A dermoscopic image of a skin lesion.
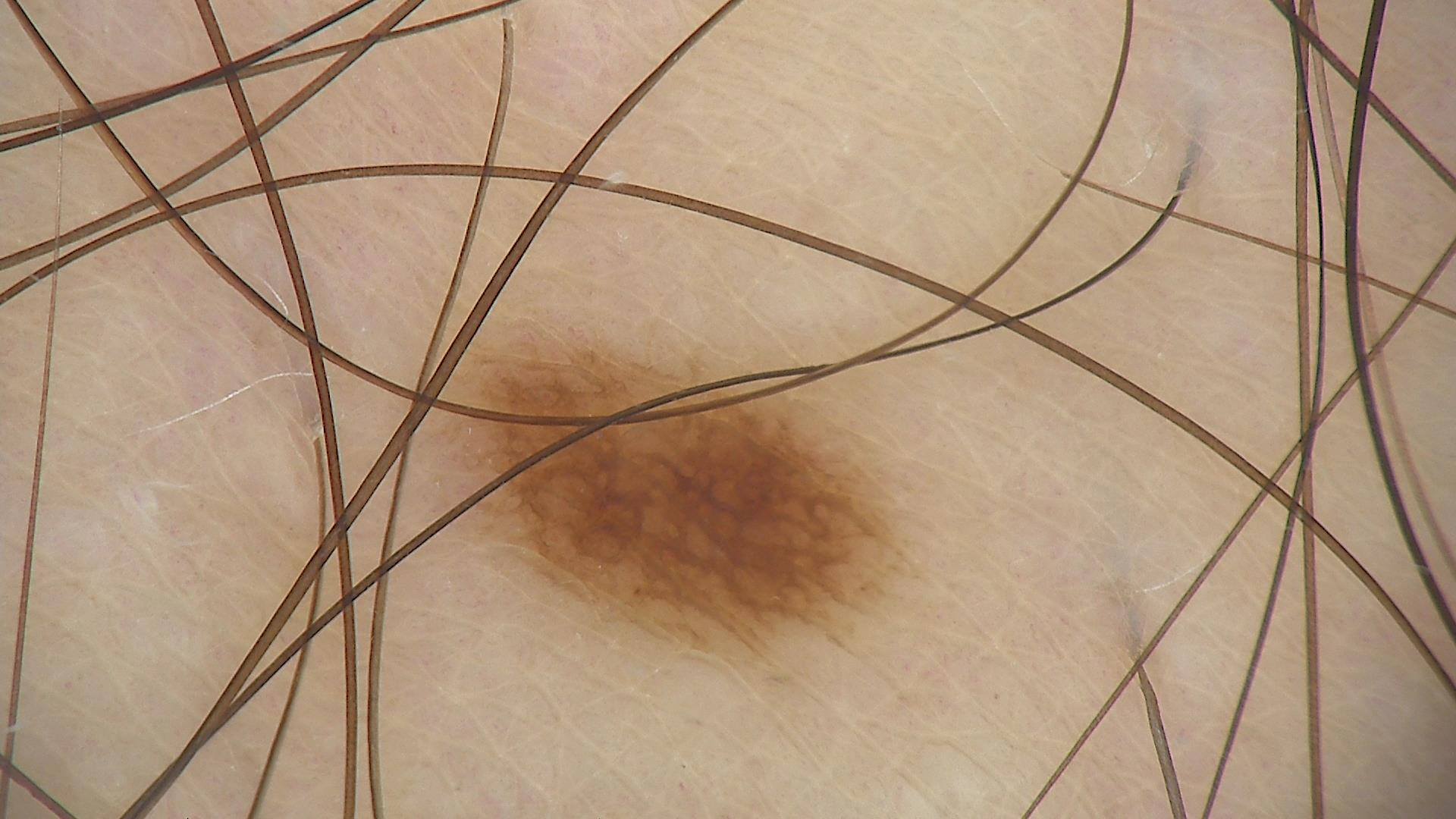– class: dysplastic junctional nevus (expert consensus)